An image taken at an angle; located on the front of the torso, arm, back of the hand and back of the torso.
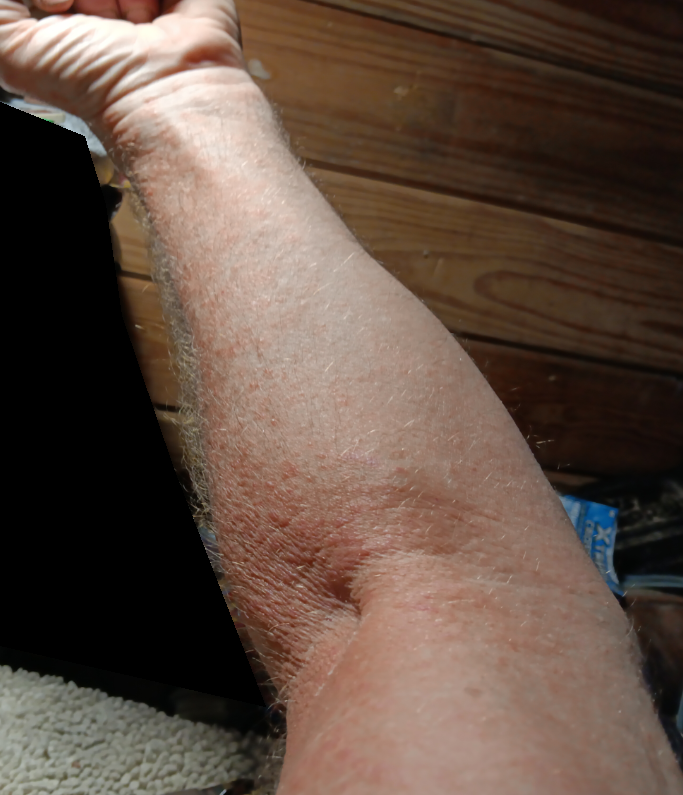assessment: unable to determine